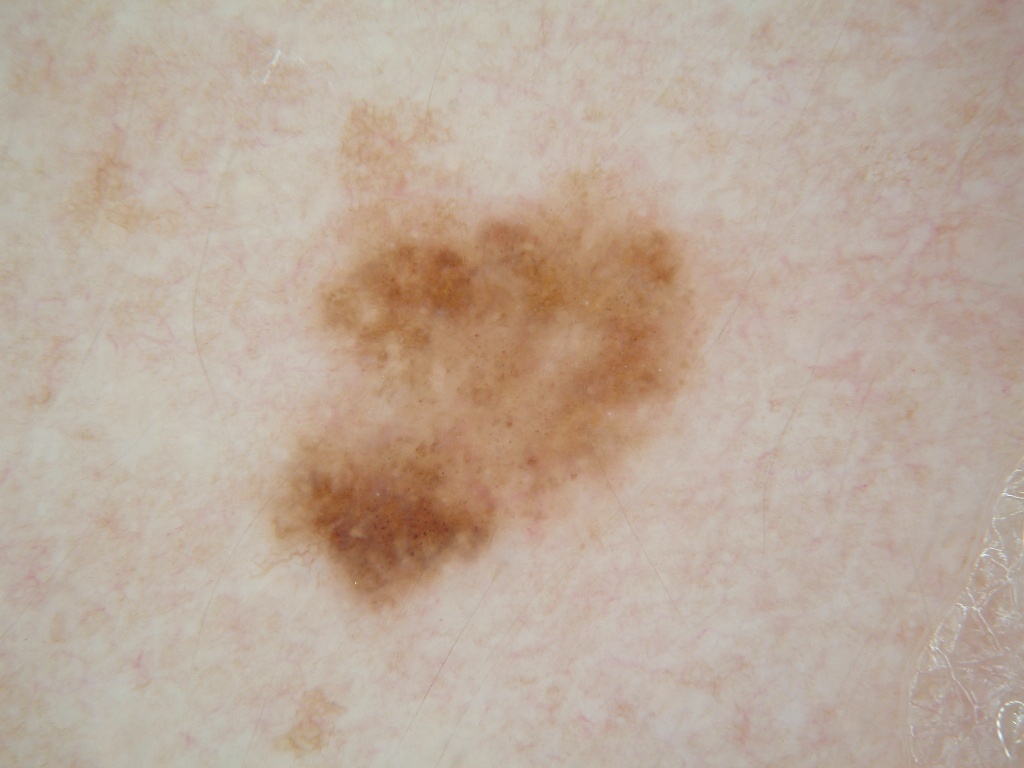This is a dermoscopic photograph of a skin lesion. The dermoscopic pattern shows milia-like cysts and pigment network. In (x1, y1, x2, y2) order, the lesion is bounded by (255, 91, 717, 626). Consistent with a melanocytic nevus, a benign skin lesion.